Dermoscopy of a skin lesion.
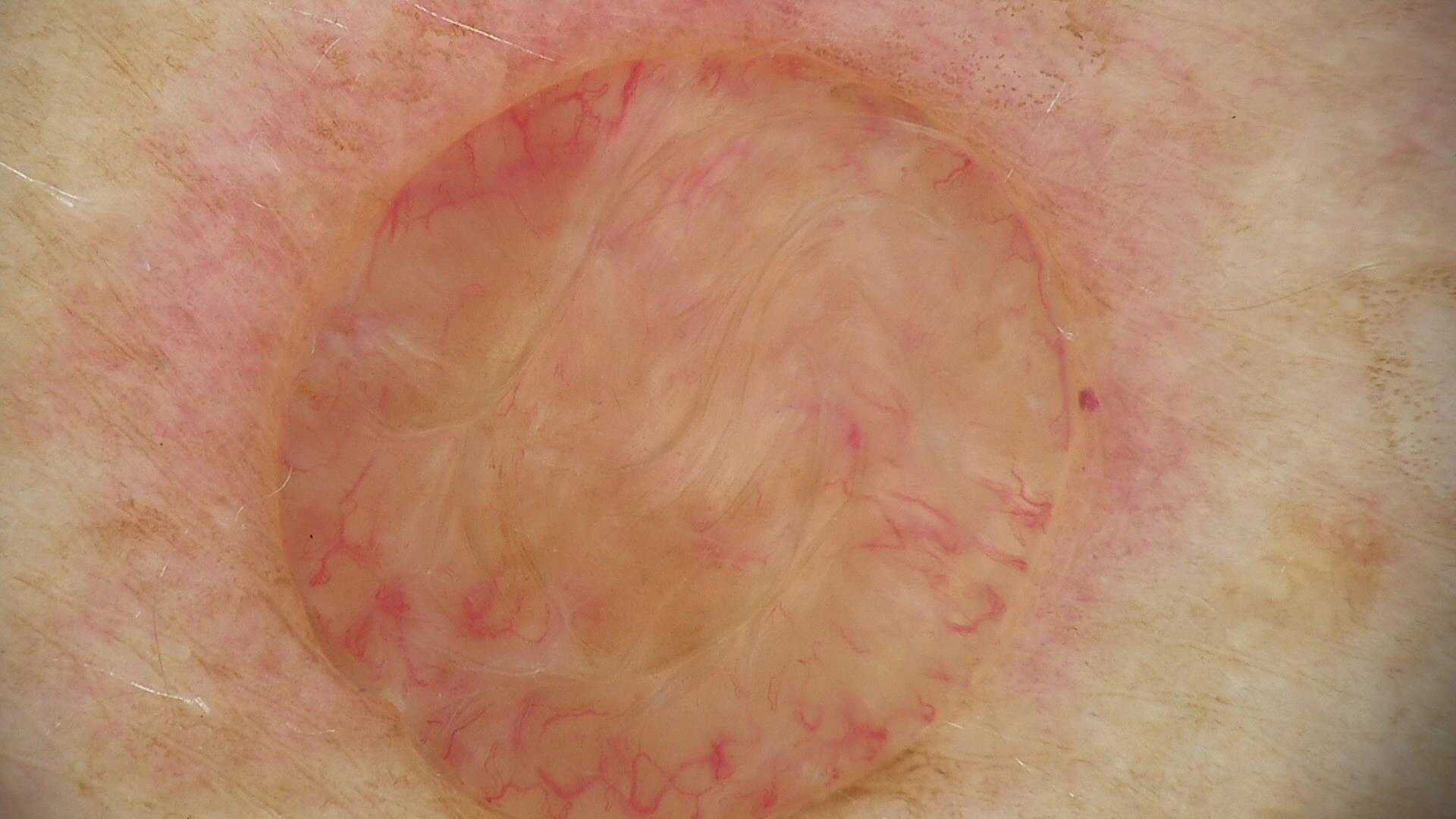The diagnostic label was a banal lesion — a dermal nevus.